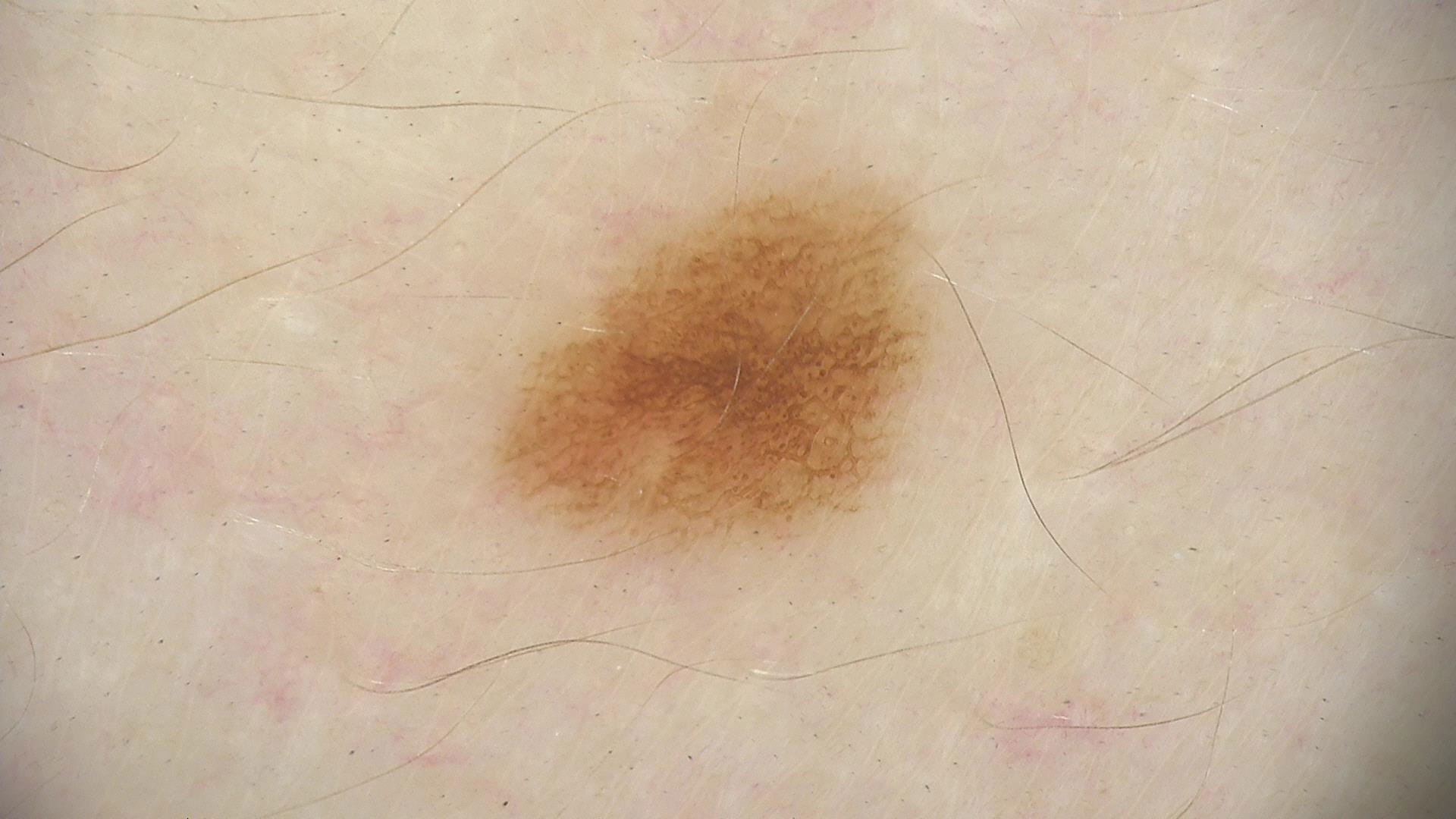Case:
A dermoscopic photograph of a skin lesion.
Conclusion:
Consistent with a benign lesion — a dysplastic junctional nevus.